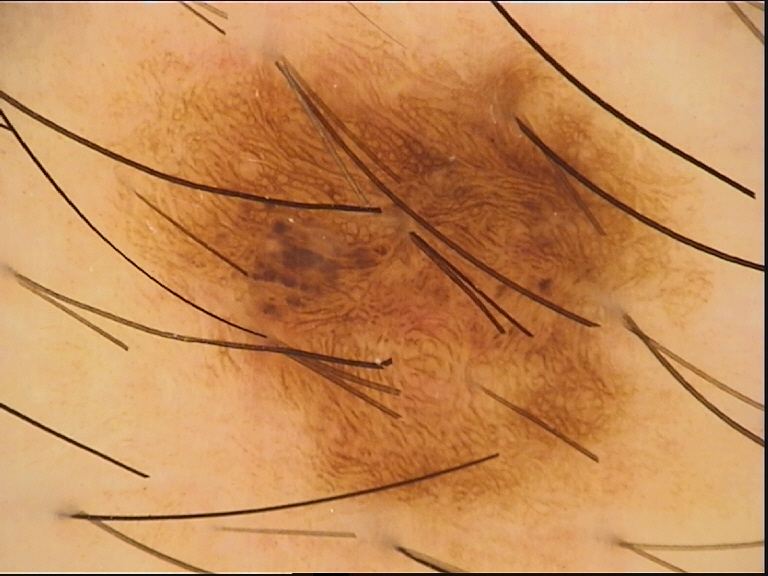Conclusion:
Labeled as a dysplastic junctional nevus.